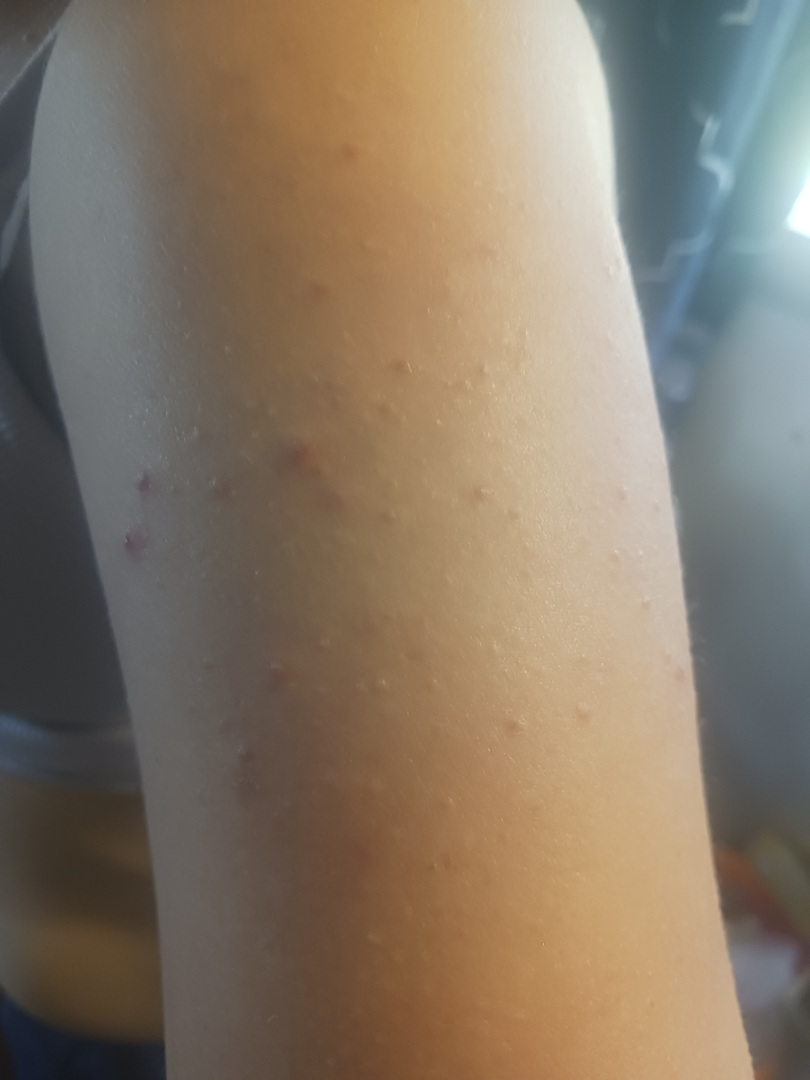The dermatologist could not determine a likely condition from the photograph alone.
The photograph is a close-up of the affected area.